Female contributor, age 18–29 · the patient considered this a rash · an image taken at a distance · the leg is involved — 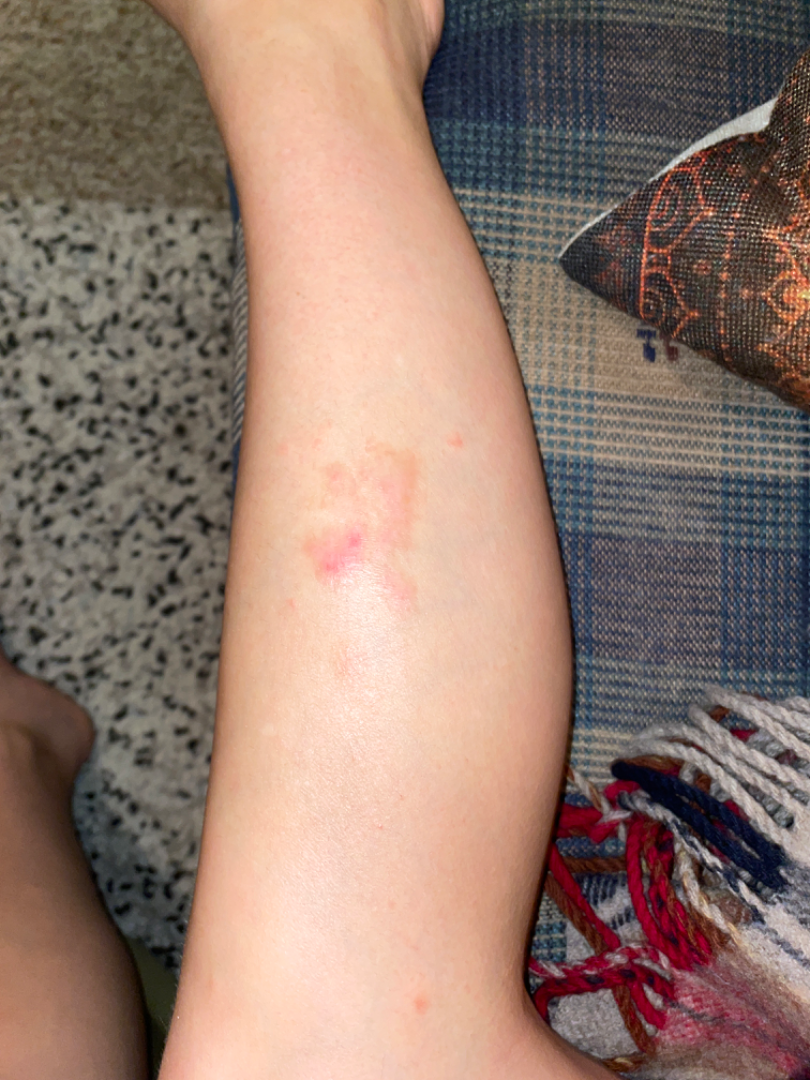Q: What is the dermatologist's impression?
A: Eczema and Lichen Simplex Chronicus were considered with similar weight